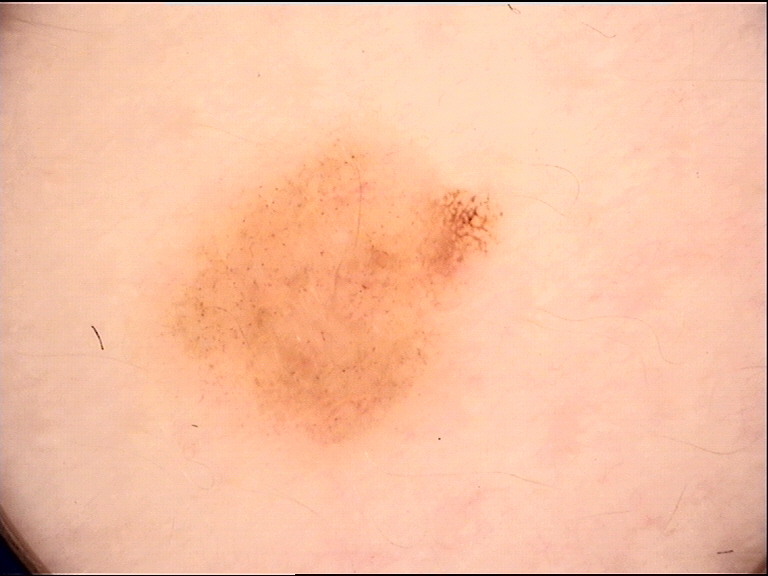A skin lesion imaged with a dermatoscope. The diagnostic label was a dysplastic junctional nevus.